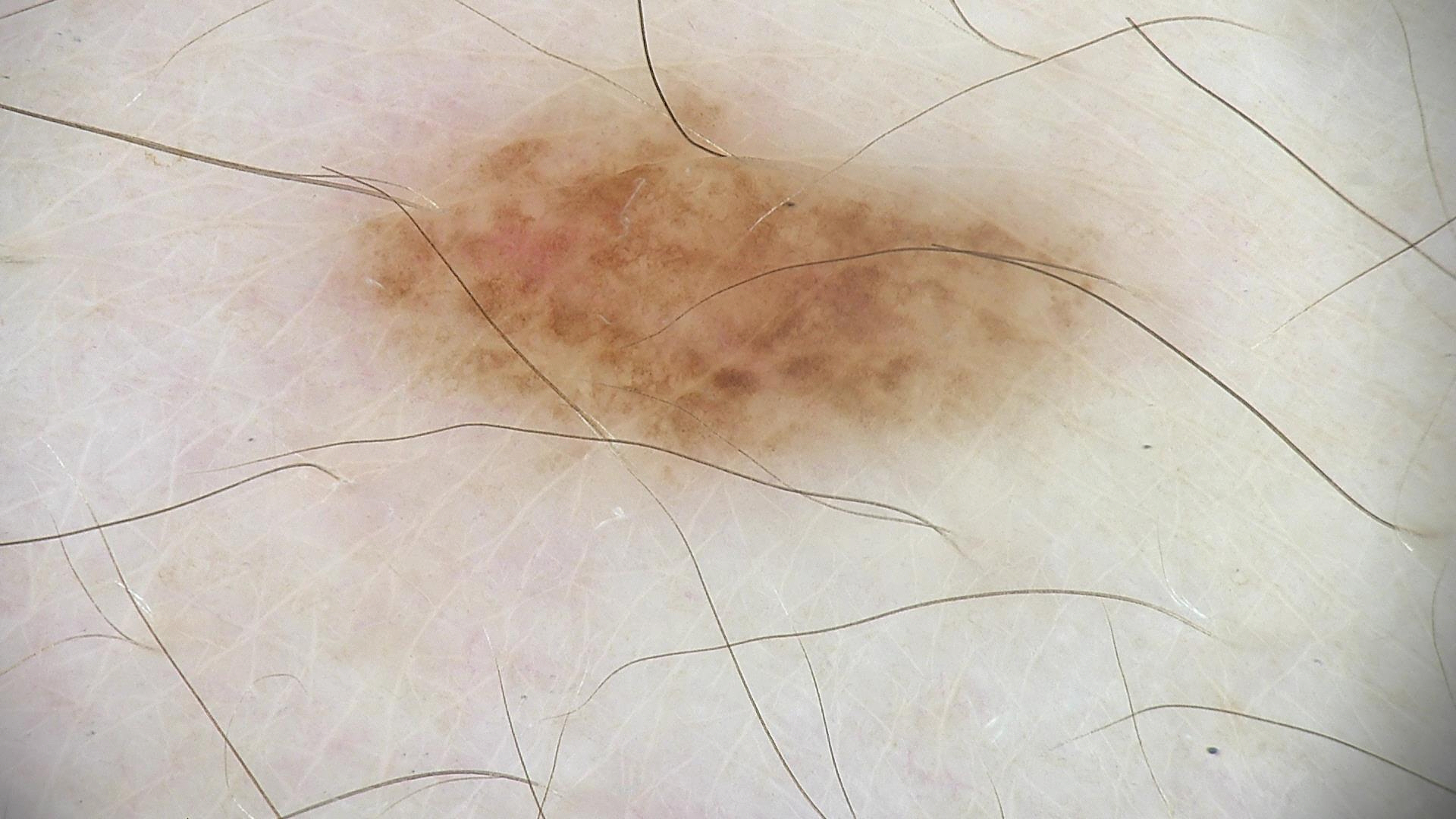The diagnosis was a dysplastic junctional nevus.